A dermoscopy image of a single skin lesion.
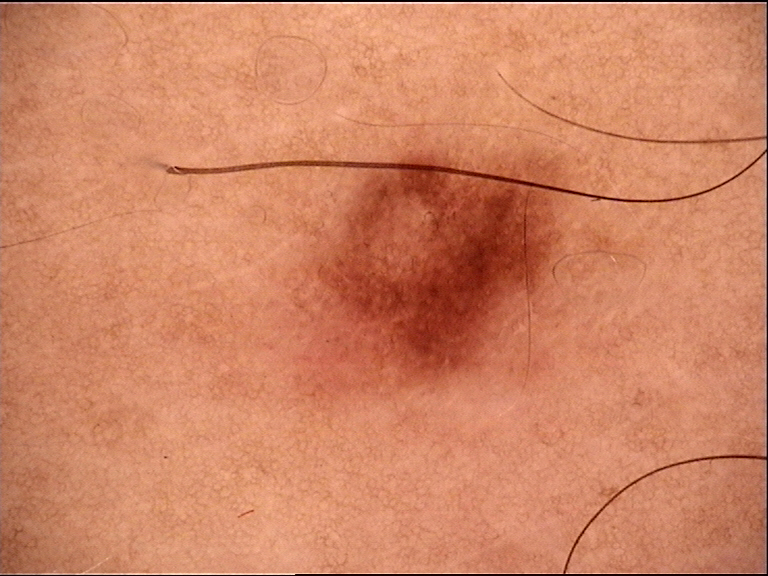Labeled as a dysplastic junctional nevus.